Close-up view:
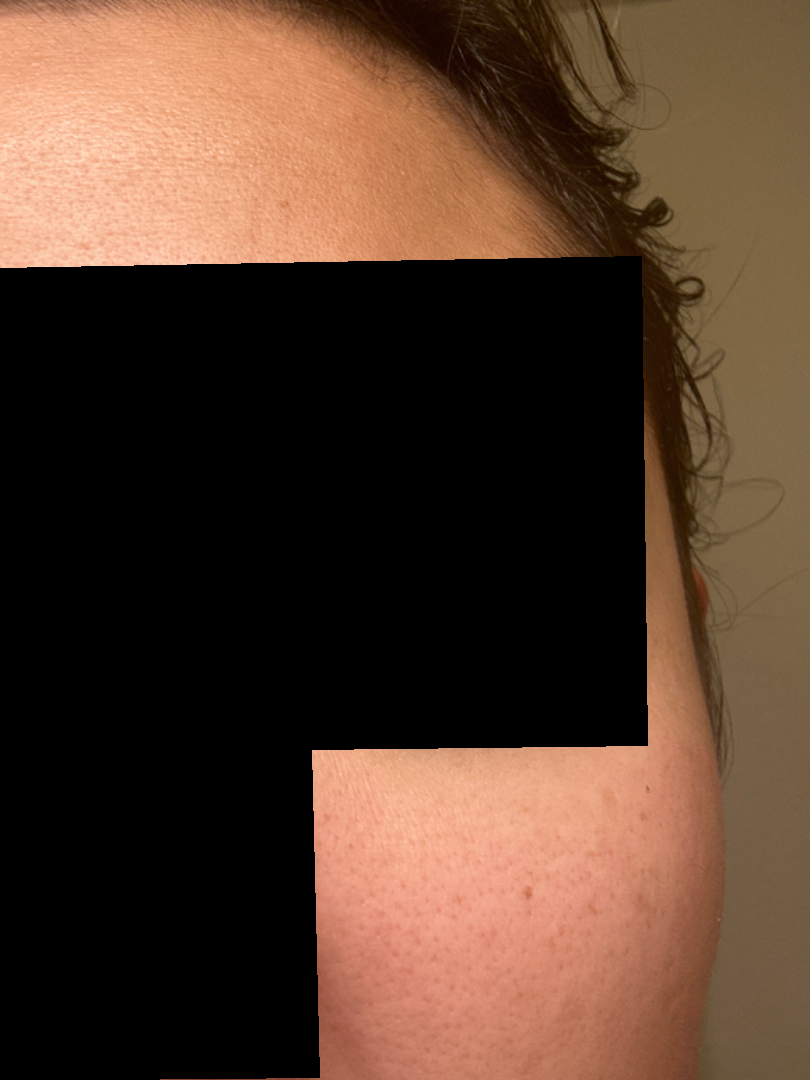Review:
No discernible skin pathology was identified on dermatologist review.